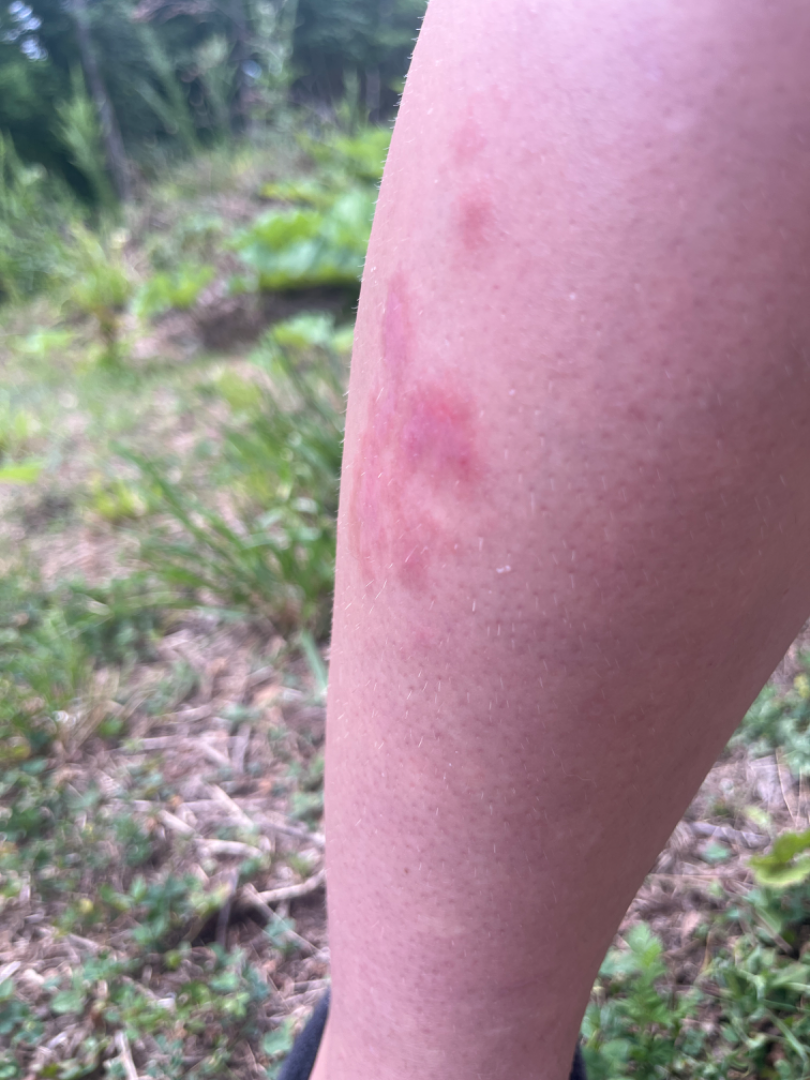The leg is involved. The contributor is a female aged 18–29. The photograph was taken at an angle. The leading consideration is Allergic Contact Dermatitis; also on the differential is Insect Bite; less likely is Eczema.